A female subject, aged approximately 70; a skin lesion imaged with a dermatoscope: 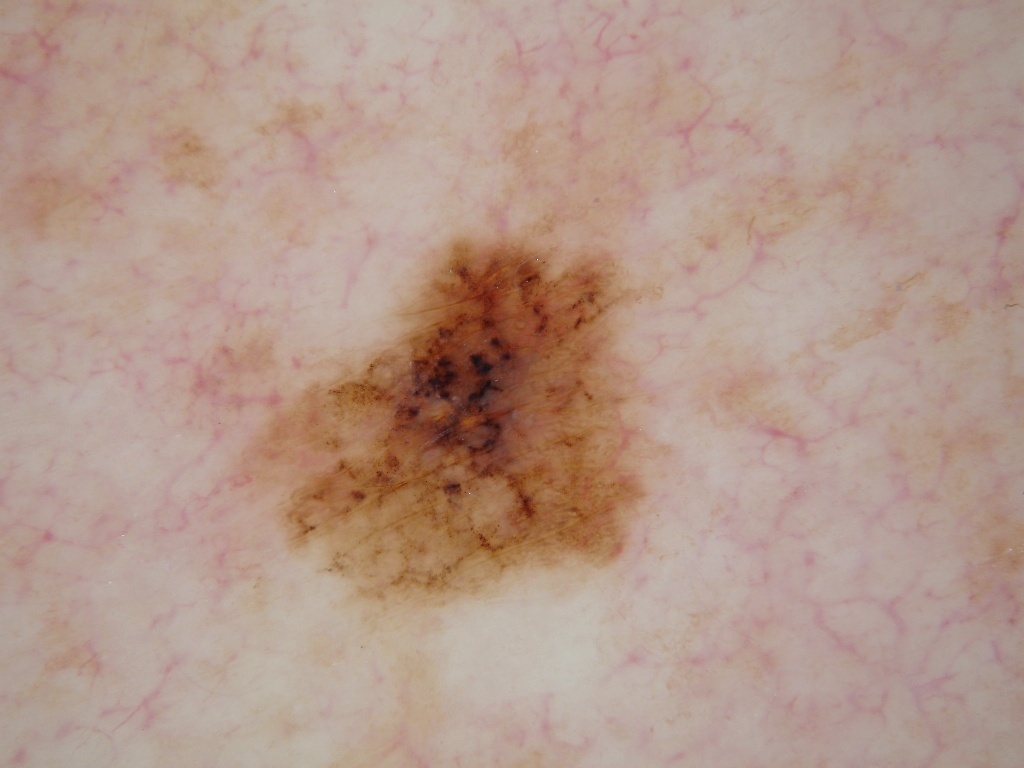lesion size: ~18% of the field | location: 224/215/676/642 | dermoscopic features assessed but absent: globules, pigment network, streaks, negative network, and milia-like cysts | impression: a melanoma.